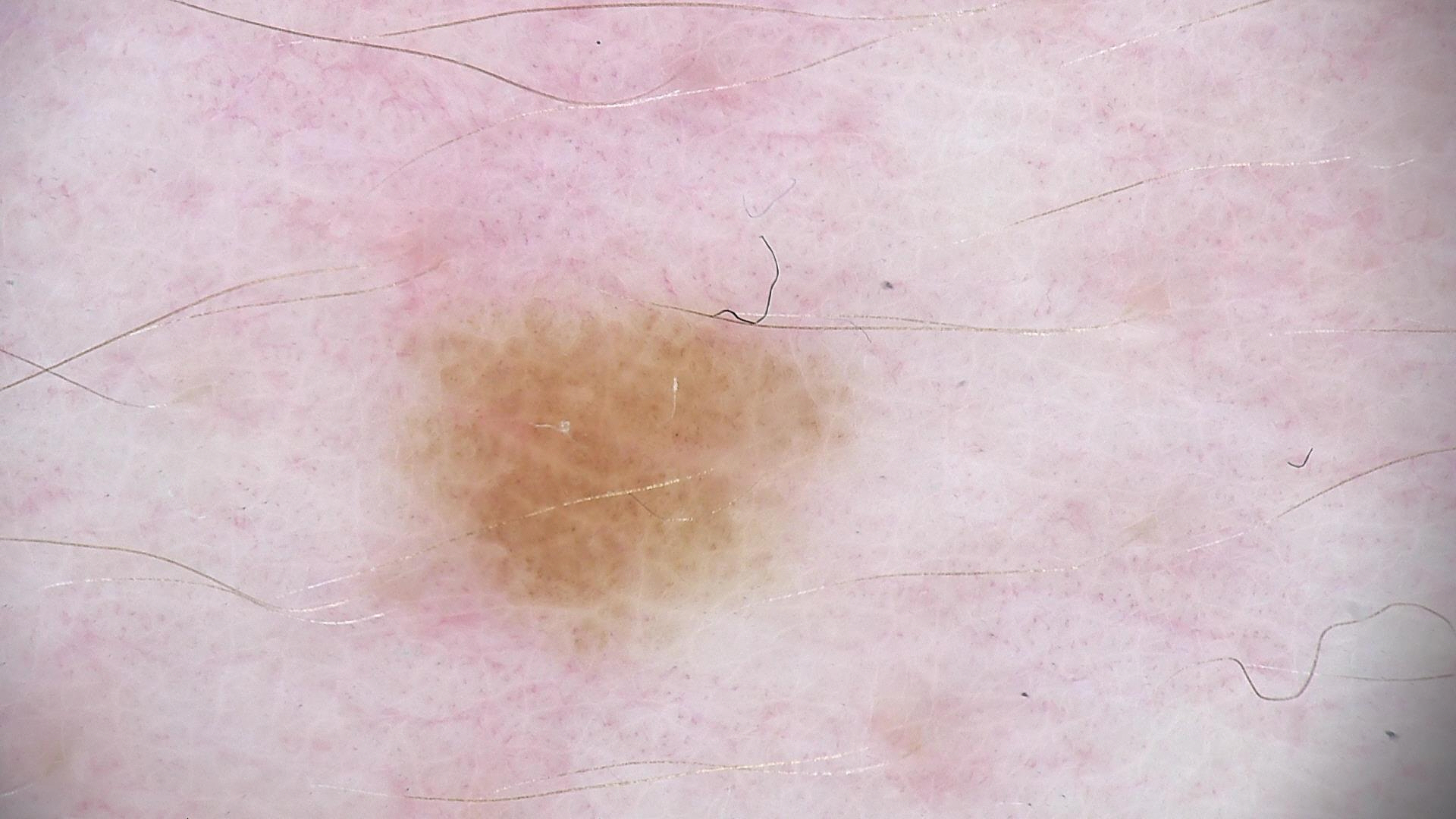* image: dermatoscopy
* class: dysplastic junctional nevus (expert consensus)